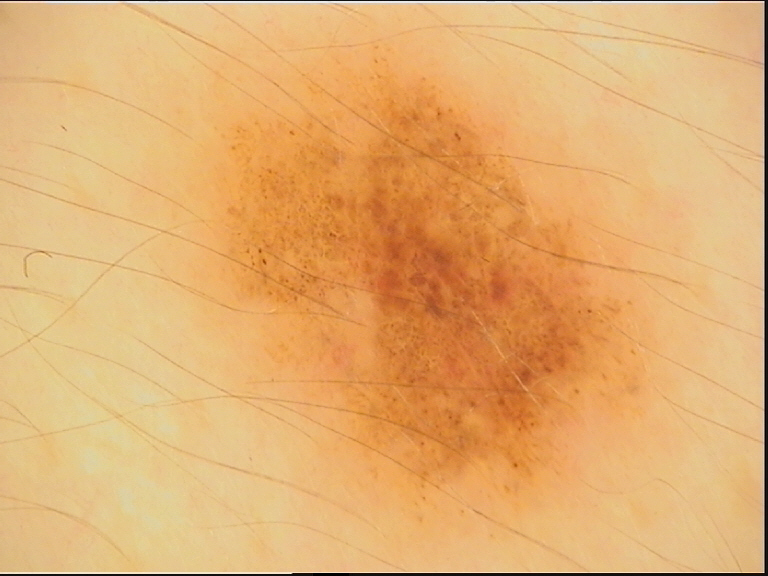Dermoscopy of a skin lesion.
Classified as a dysplastic junctional nevus.